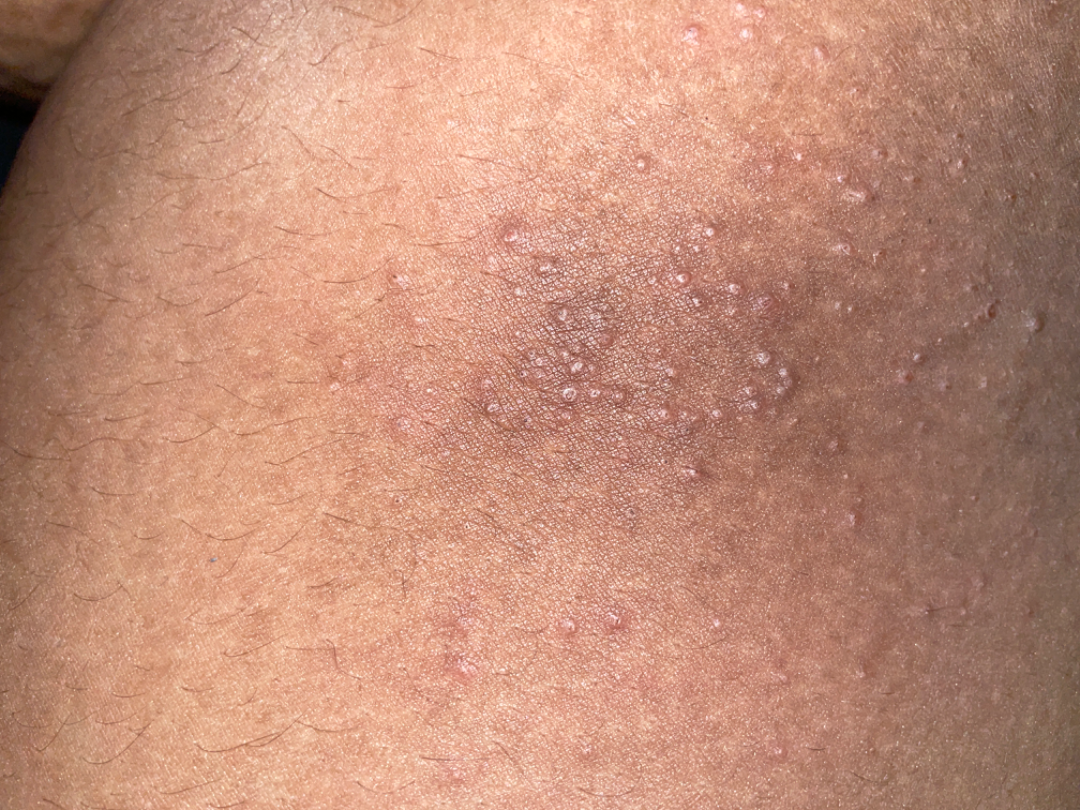• assessment — indeterminate